The patient describes having numerous moles · the patient says their skin reddens with sun exposure · imaged for a research study, with no referral diagnosis recorded · a dermatoscopic image of a skin lesion — 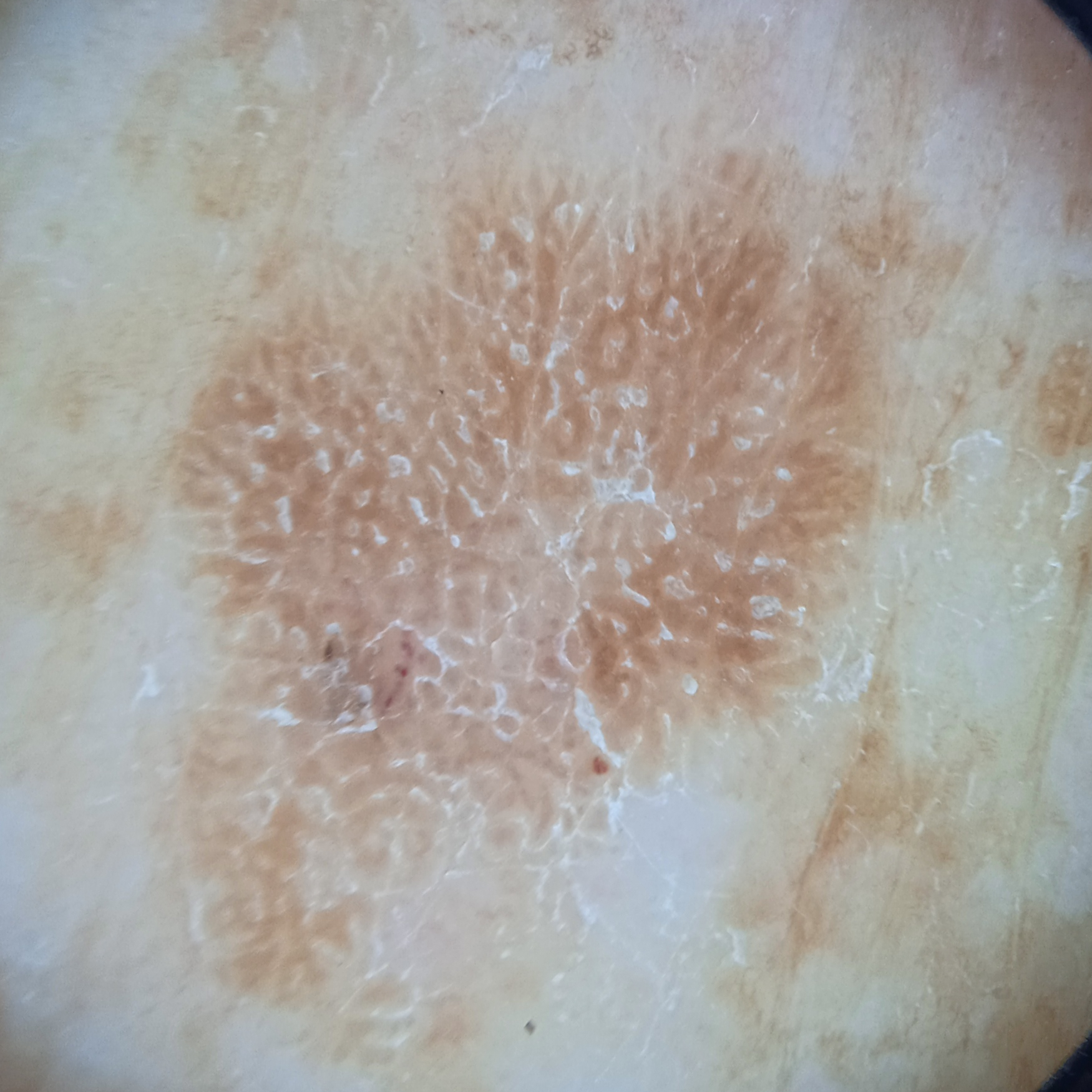The lesion is located on the back. The lesion is about 10.7 mm across. The diagnostic impression was a seborrheic keratosis.